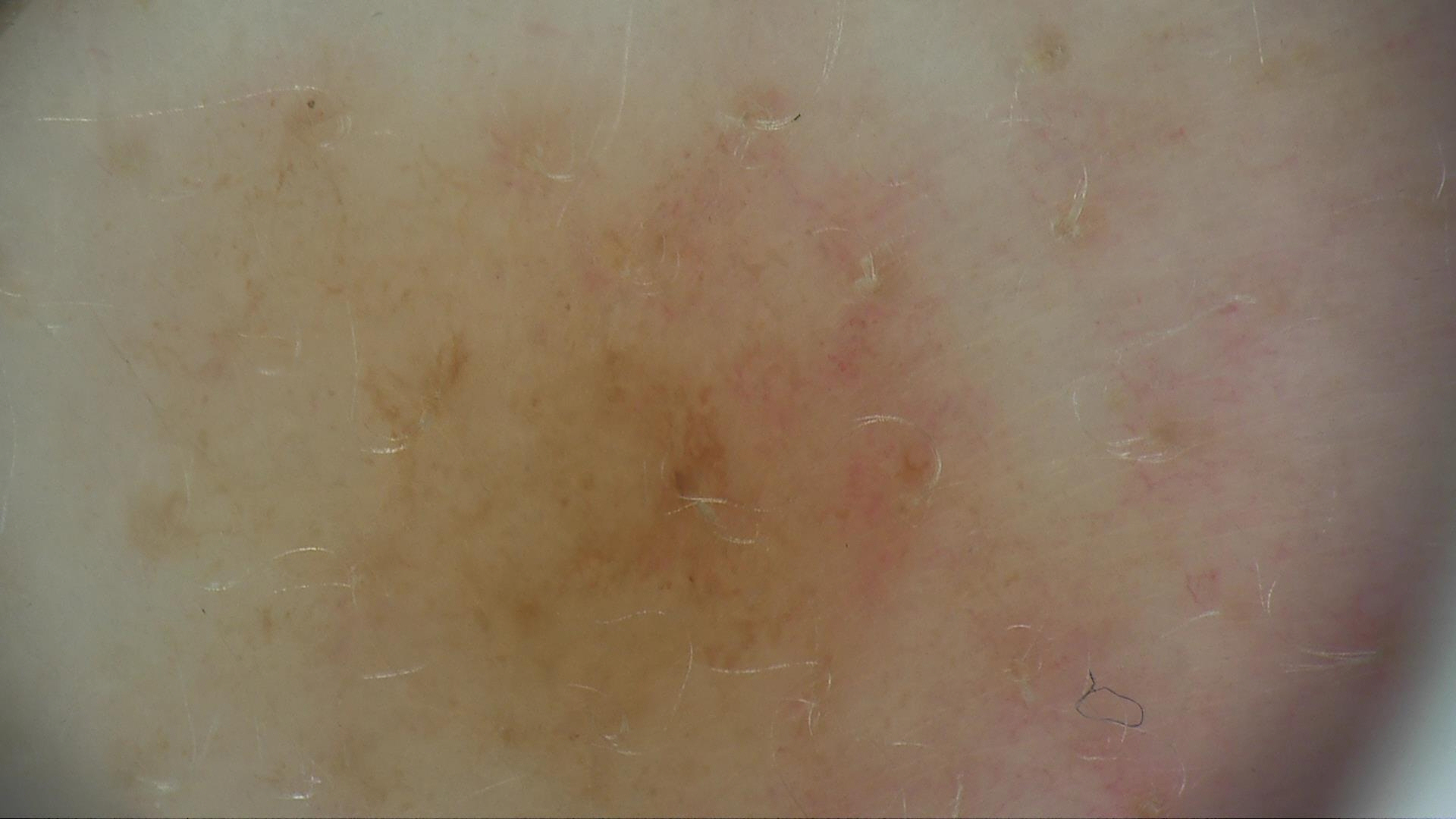<dermoscopy>
  <diagnosis>
    <name>dysplastic junctional nevus</name>
    <code>jd</code>
    <malignancy>benign</malignancy>
    <super_class>melanocytic</super_class>
    <confirmation>expert consensus</confirmation>
  </diagnosis>
</dermoscopy>